Reported lesion symptoms include bothersome appearance. The lesion is described as flat. An image taken at an angle. The subject is 40–49, female. The affected area is the leg. No associated systemic symptoms reported. The patient considered this a rash. Reported duration is one to four weeks:
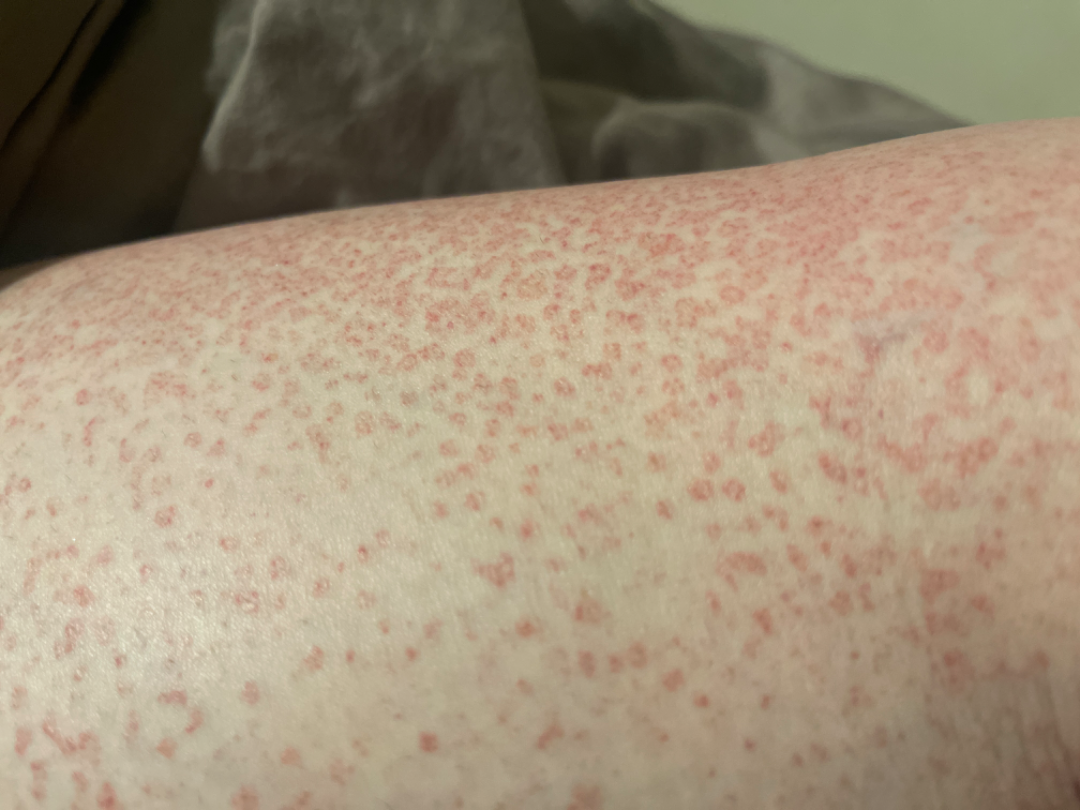  differential:
    leading:
      - Leukocytoclastic Vasculitis
    considered:
      - Pigmented purpuric eruption
    unlikely:
      - Hypersensitivity